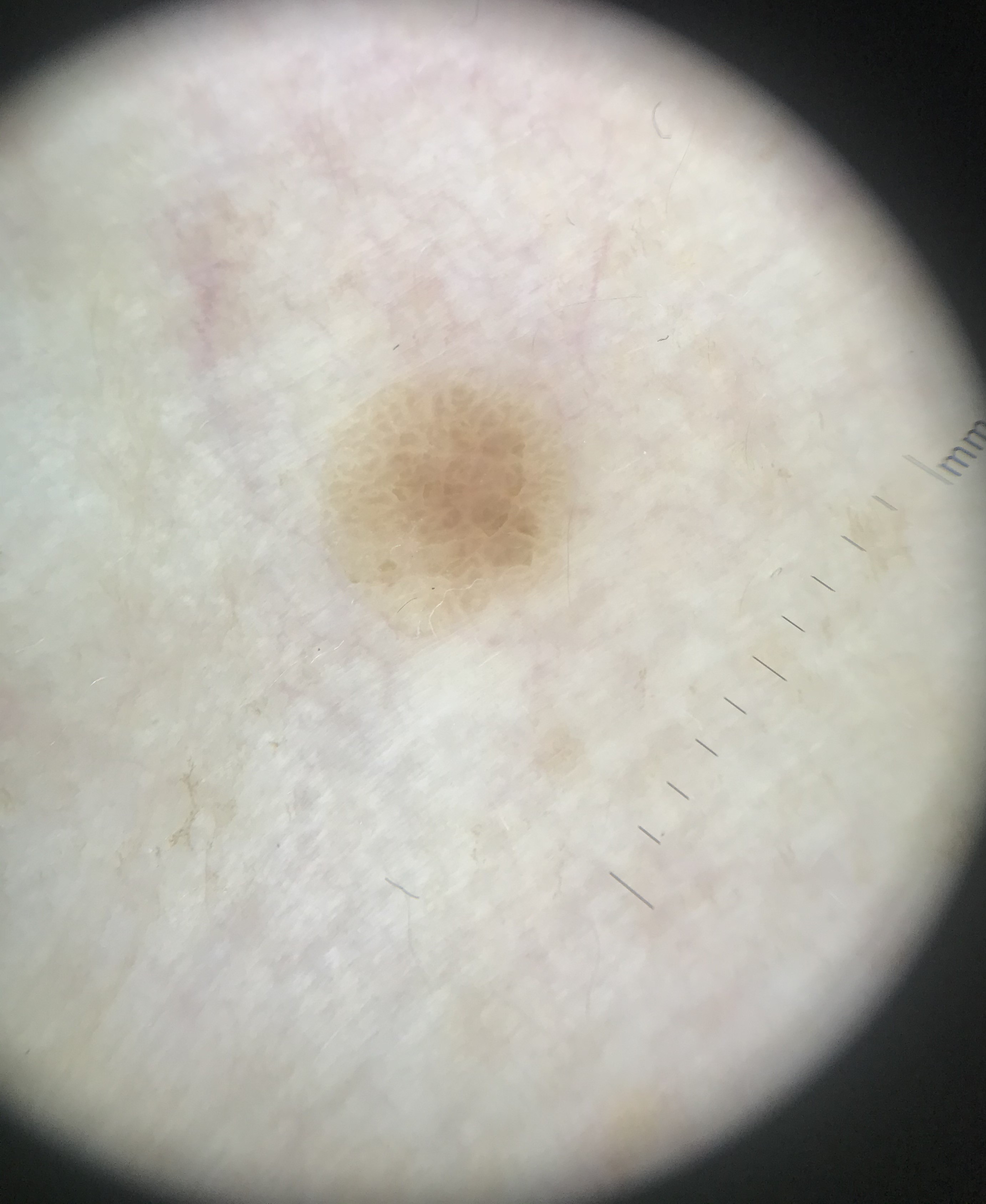Findings:
• modality · dermatoscopy
• category · keratinocytic
• label · seborrheic keratosis (expert consensus)